The patient was assessed as Fitzpatrick phototype II · a female patient in their 60s: 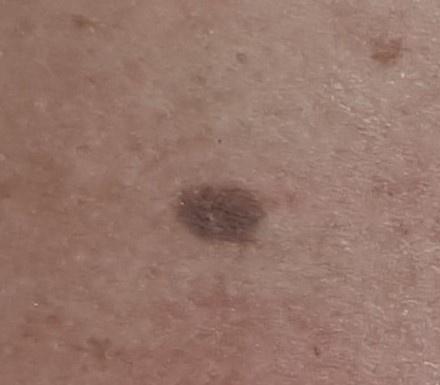| feature | finding |
|---|---|
| anatomic site | the trunk (the posterior trunk) |
| pathology | Nevus (biopsy-proven) |